A patient in their 50s:
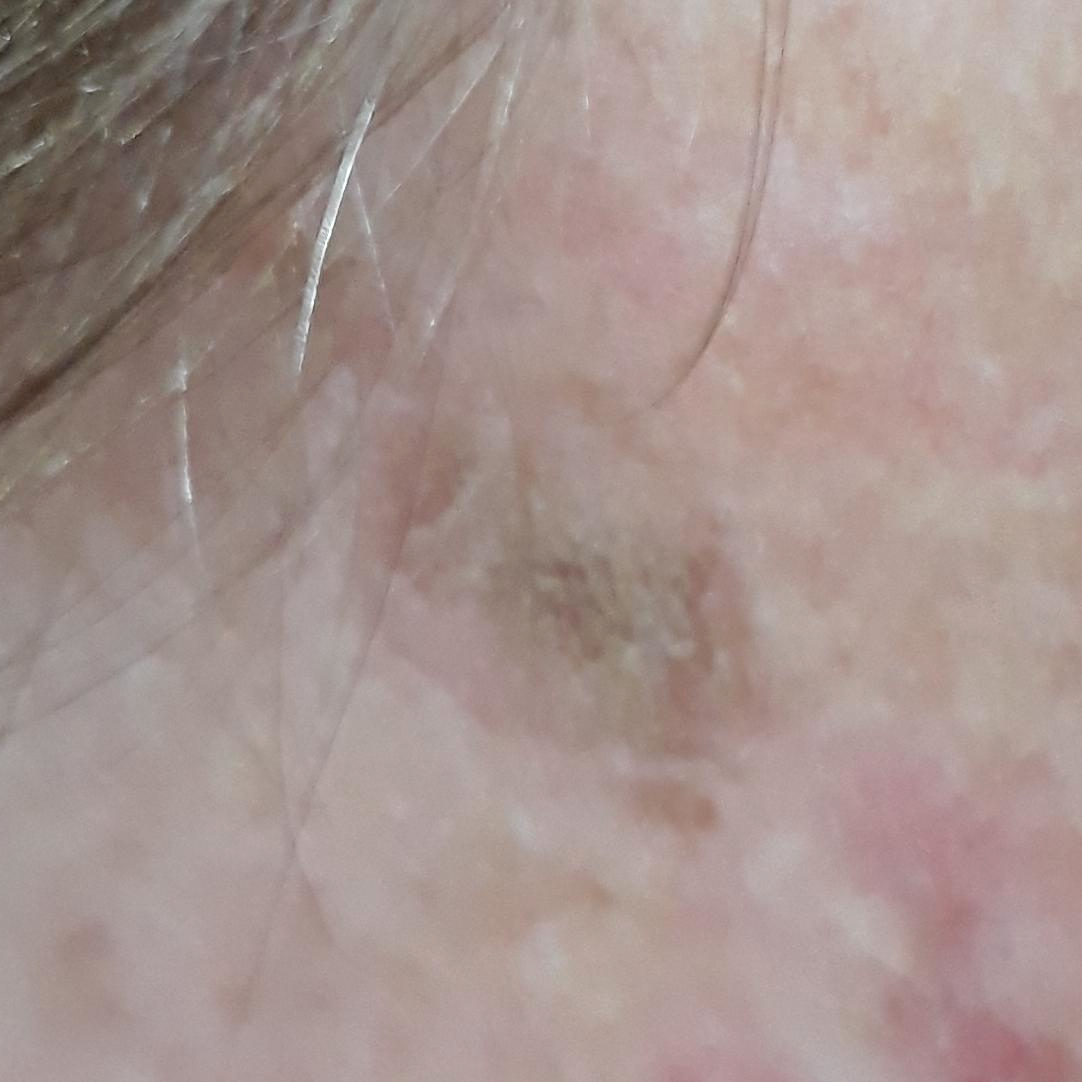Notes:
* site — the face
* diagnosis — seborrheic keratosis (clinical consensus)